A dermoscopic image of a skin lesion.
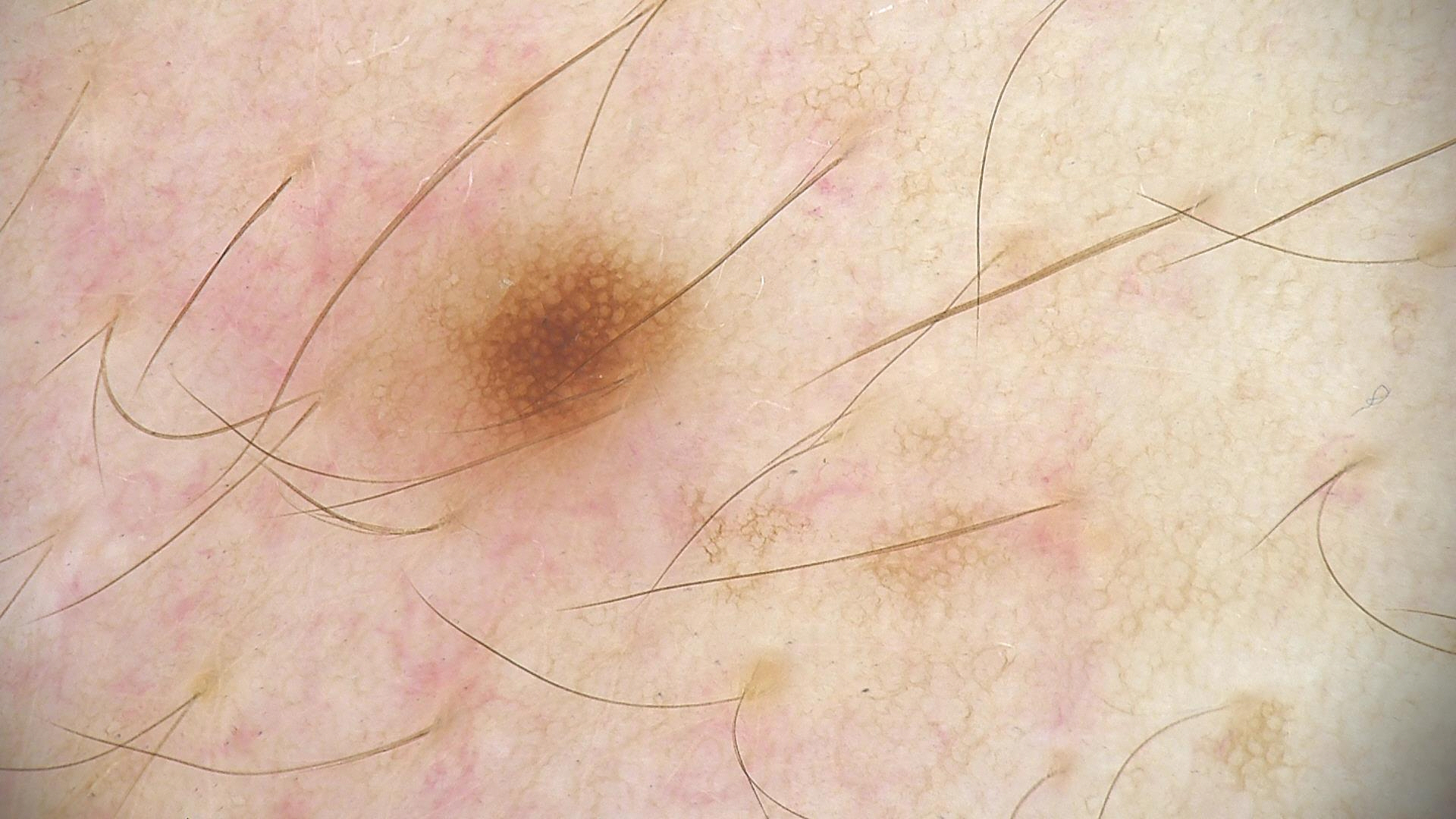classification = banal; diagnosis = junctional nevus (expert consensus).